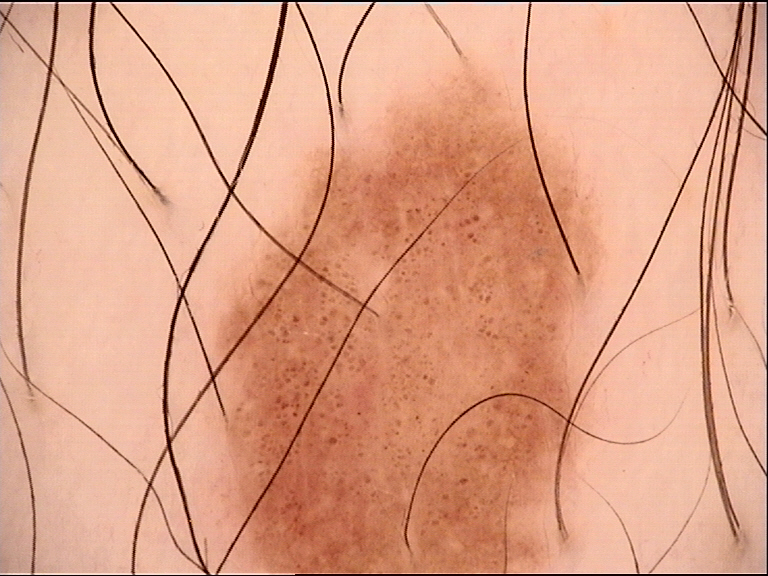| field | value |
|---|---|
| label | dysplastic junctional nevus (expert consensus) |